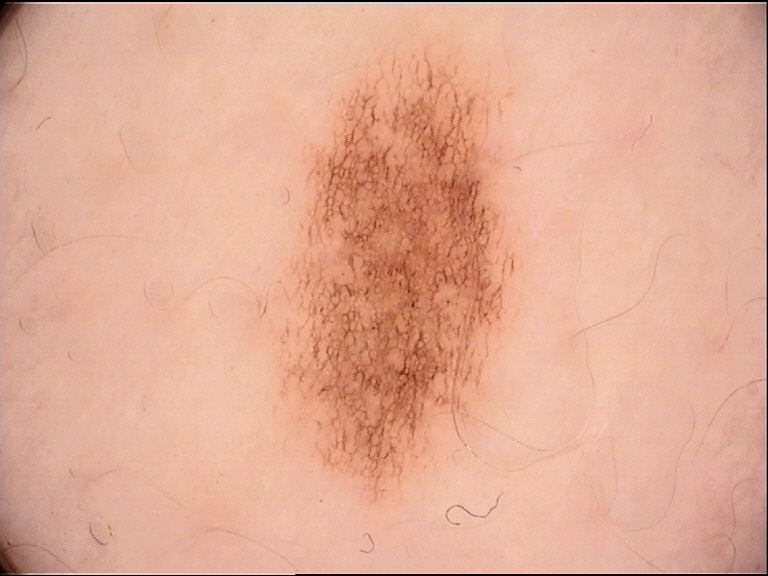A dermoscopy image of a single skin lesion. The diagnosis was a benign lesion — a dysplastic junctional nevus.